A skin lesion imaged with a dermatoscope.
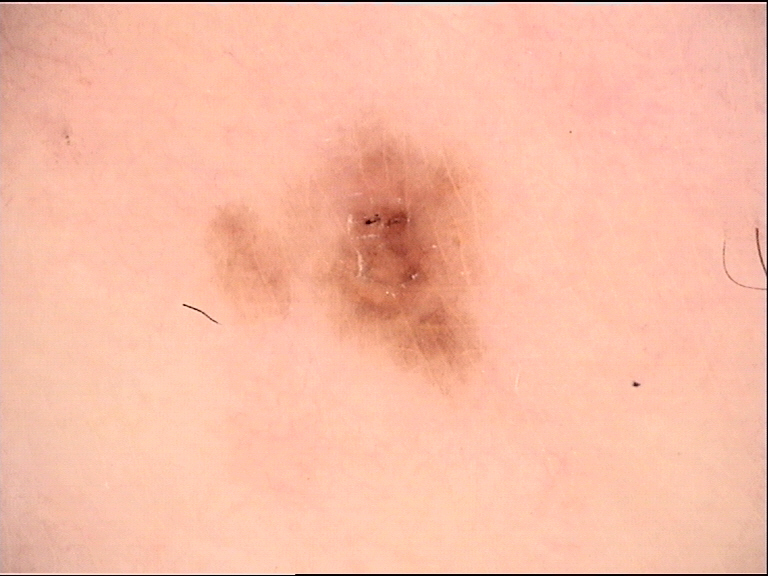Q: What was the diagnostic impression?
A: dysplastic junctional nevus (expert consensus)